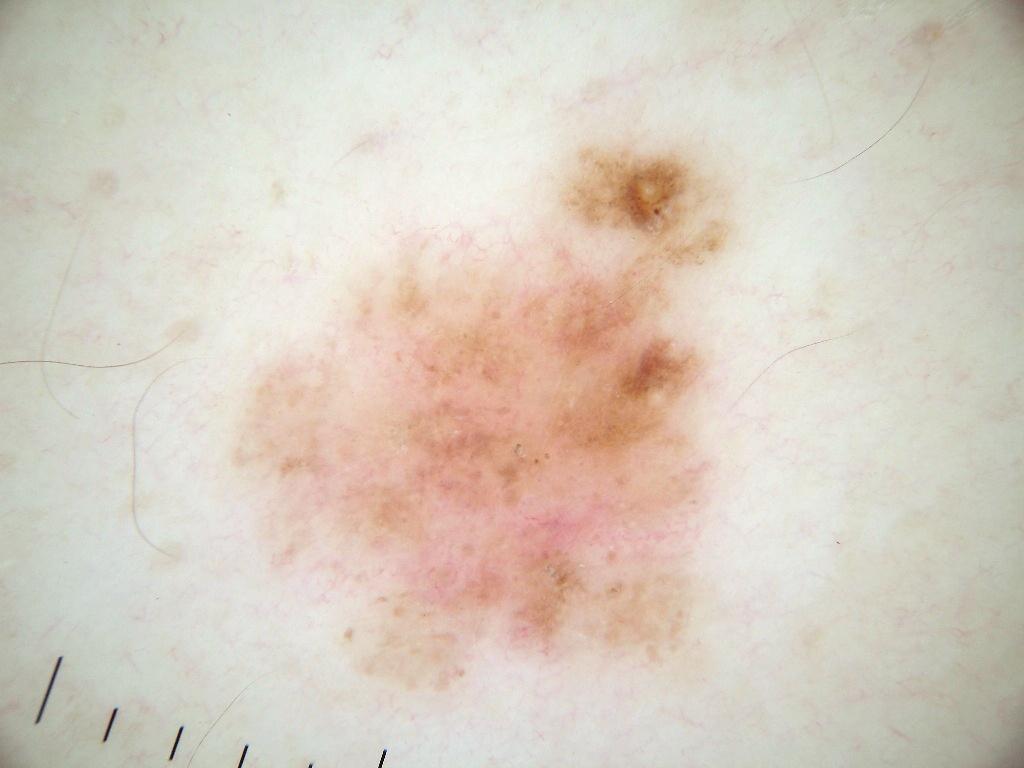image:
  modality: dermoscopy
patient:
  sex: male
  age_approx: 50
lesion_location:
  bbox_xyxy:
    - 211
    - 116
    - 761
    - 722
dermoscopic_features:
  present:
    - globules
  absent:
    - negative network
    - streaks
    - pigment network
    - milia-like cysts
diagnosis:
  name: melanocytic nevus
  malignancy: benign
  lineage: melanocytic
  provenance: clinical